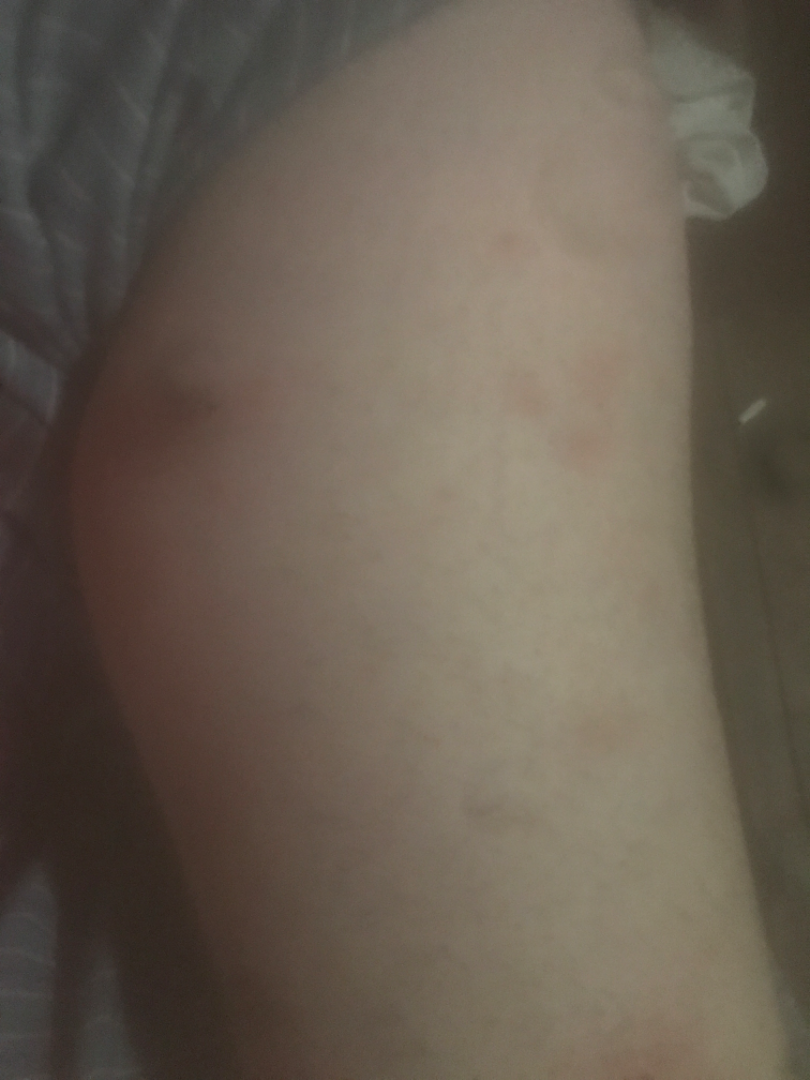assessment: indeterminate
site: leg
contributor: female, age 30–39
image framing: at an angle